A skin lesion imaged with a dermatoscope.
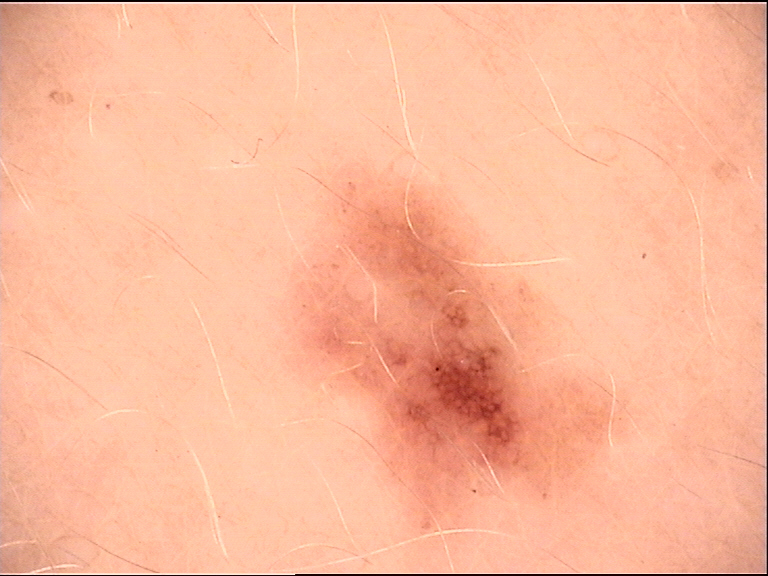The diagnosis was a benign lesion — a dysplastic junctional nevus.